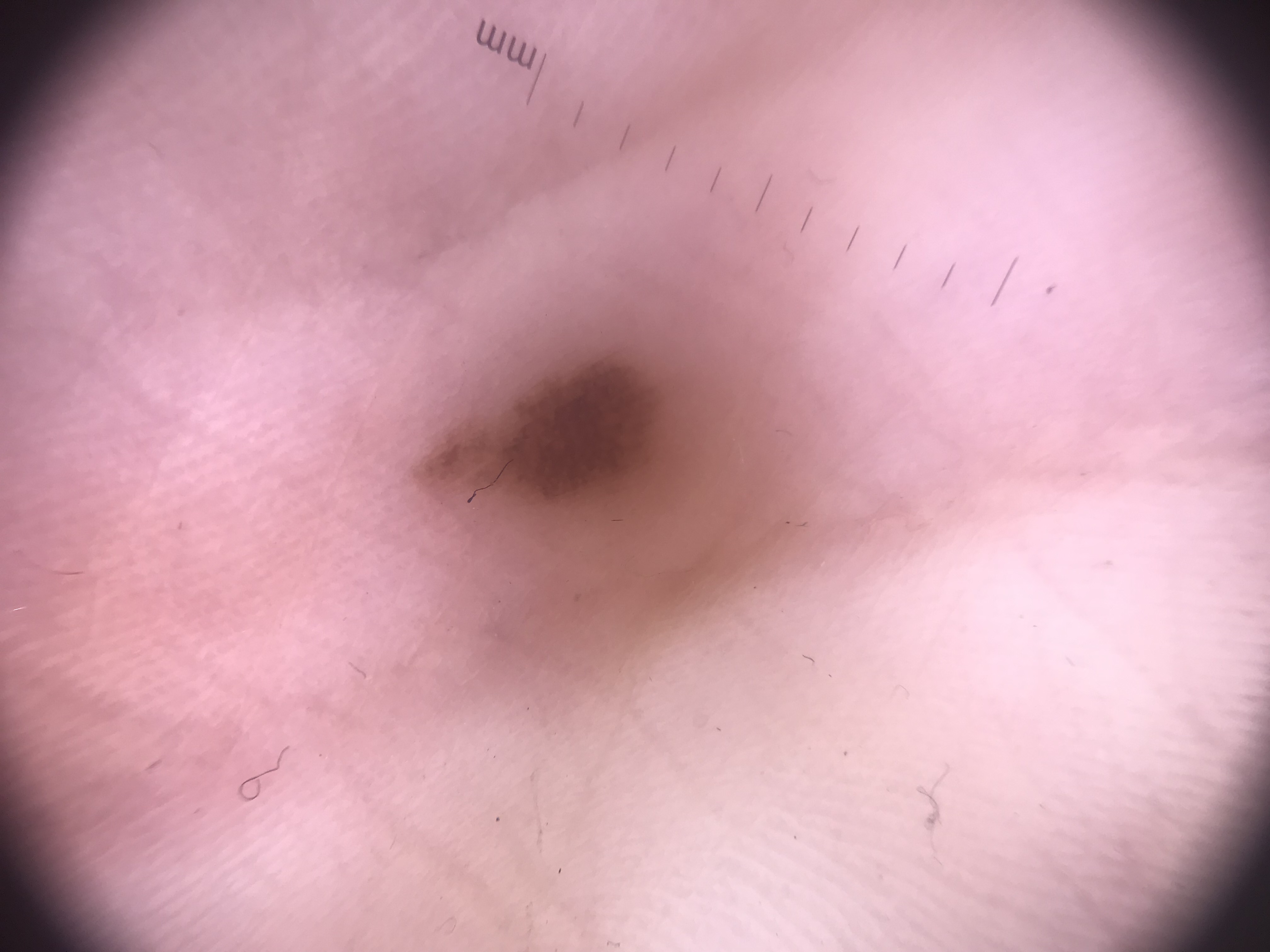Findings:
– label · acral junctional nevus (expert consensus)